The photo was captured at a distance. Located on the leg. The patient is 18–29, female: 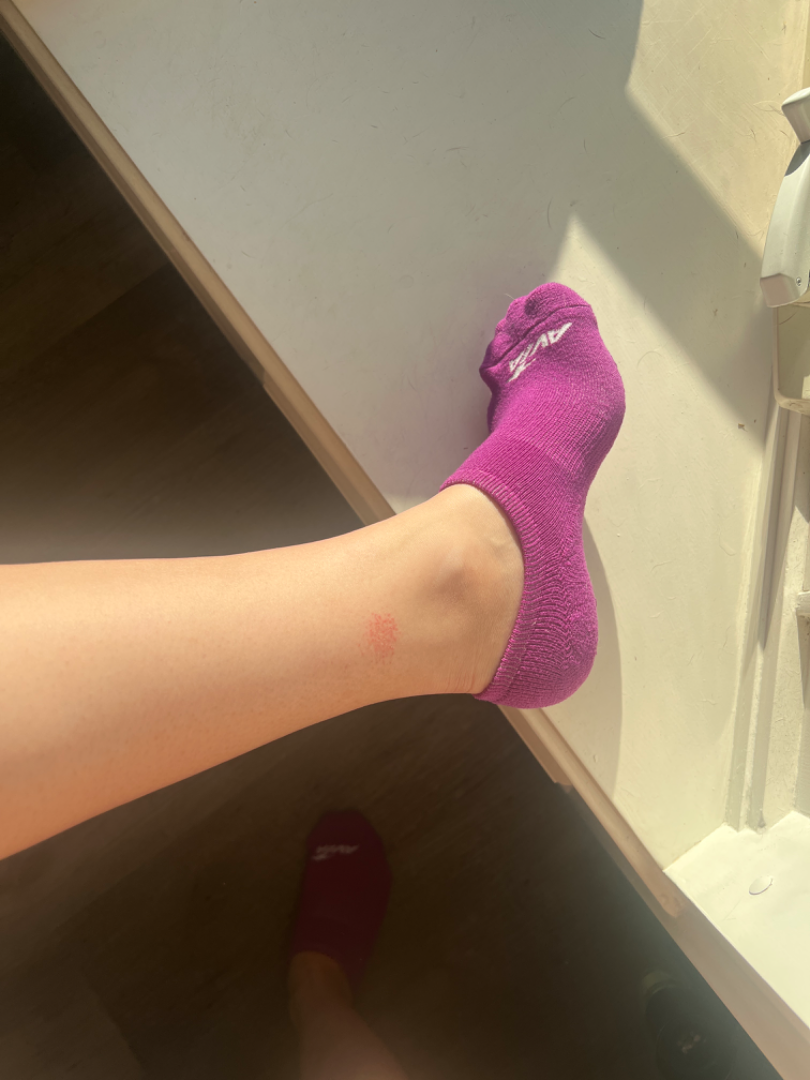Q: What is the dermatologist's impression?
A: reviewed remotely by three dermatologists: the leading consideration is Eczema; possibly Irritant Contact Dermatitis; less likely is Acute dermatitis, NOS; less probable is Tinea; a remote consideration is Allergic Contact Dermatitis